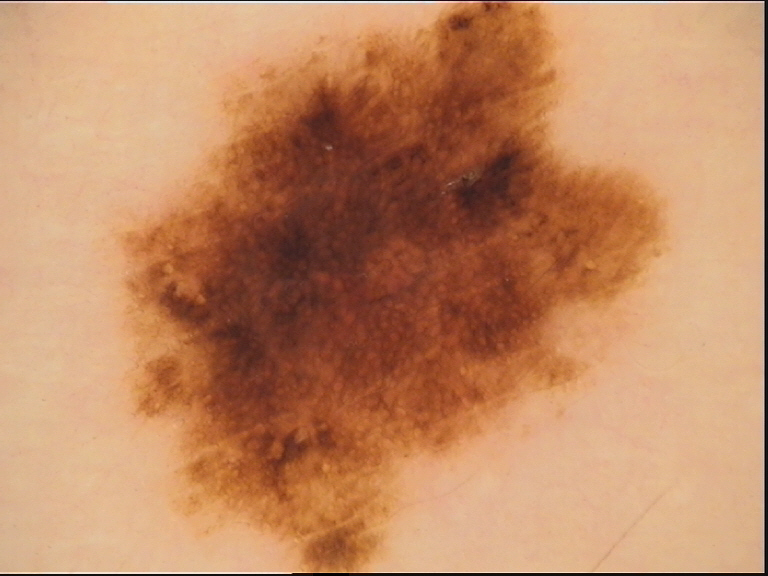  image: dermatoscopy
  diagnosis:
    name: dysplastic compound nevus
    code: cd
    malignancy: benign
    super_class: melanocytic
    confirmation: expert consensus